Close-up view.
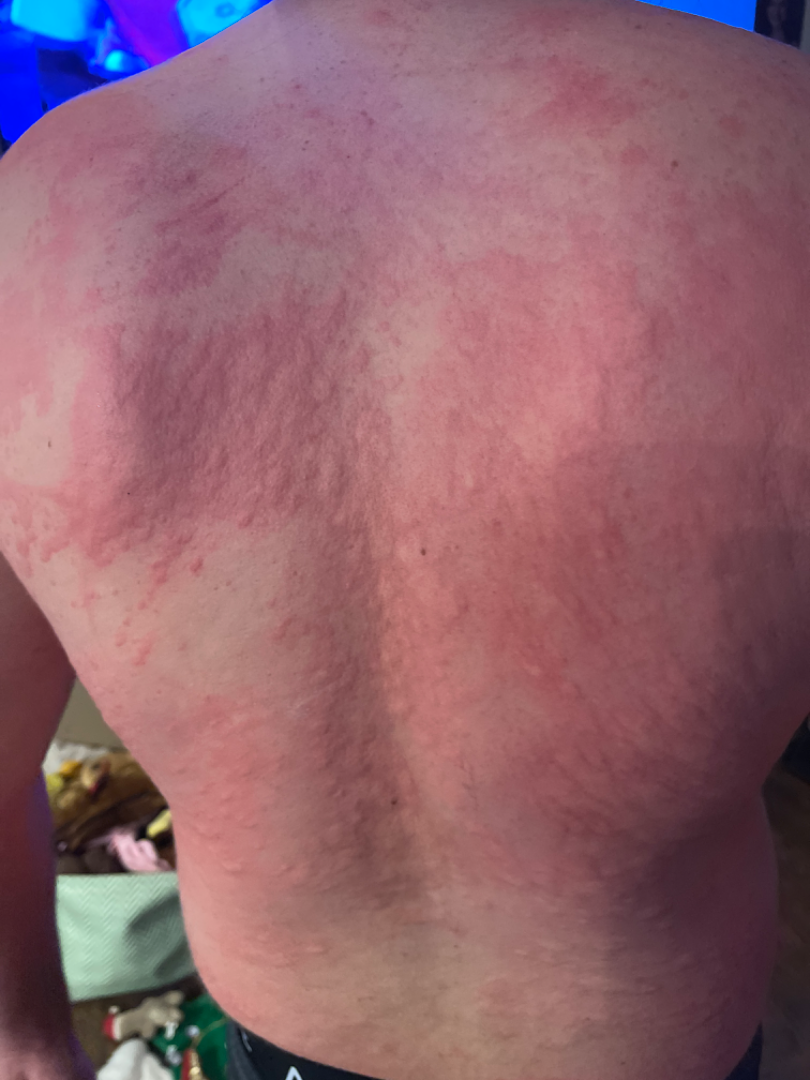On photographic review by a dermatologist: consistent with Urticaria.